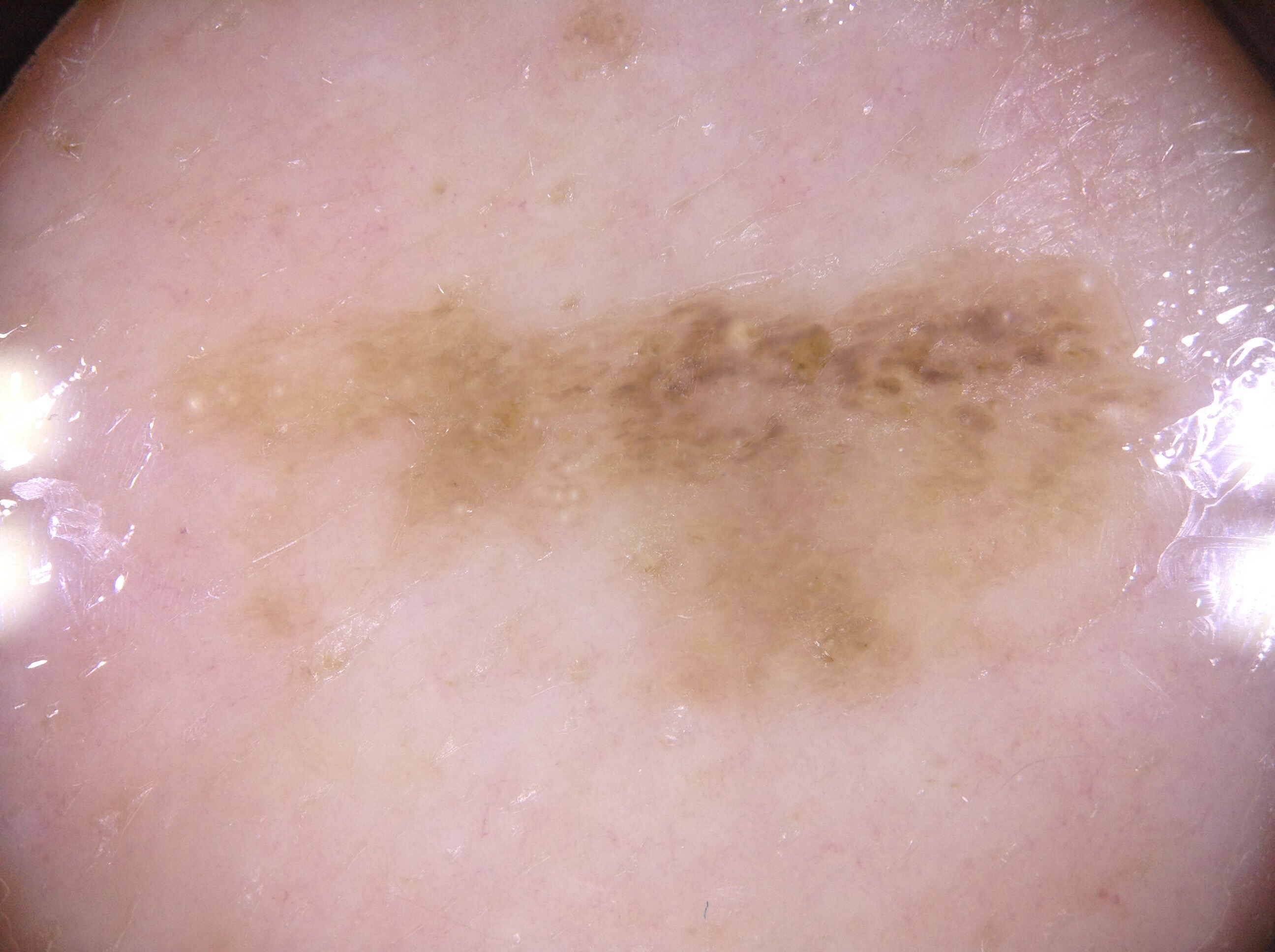image=dermoscopy | patient=male, aged 73 to 77 | extent=~22% of the field | bounding box=(155, 235, 1170, 723) | dermoscopic findings=milia-like cysts | diagnosis=a seborrheic keratosis.